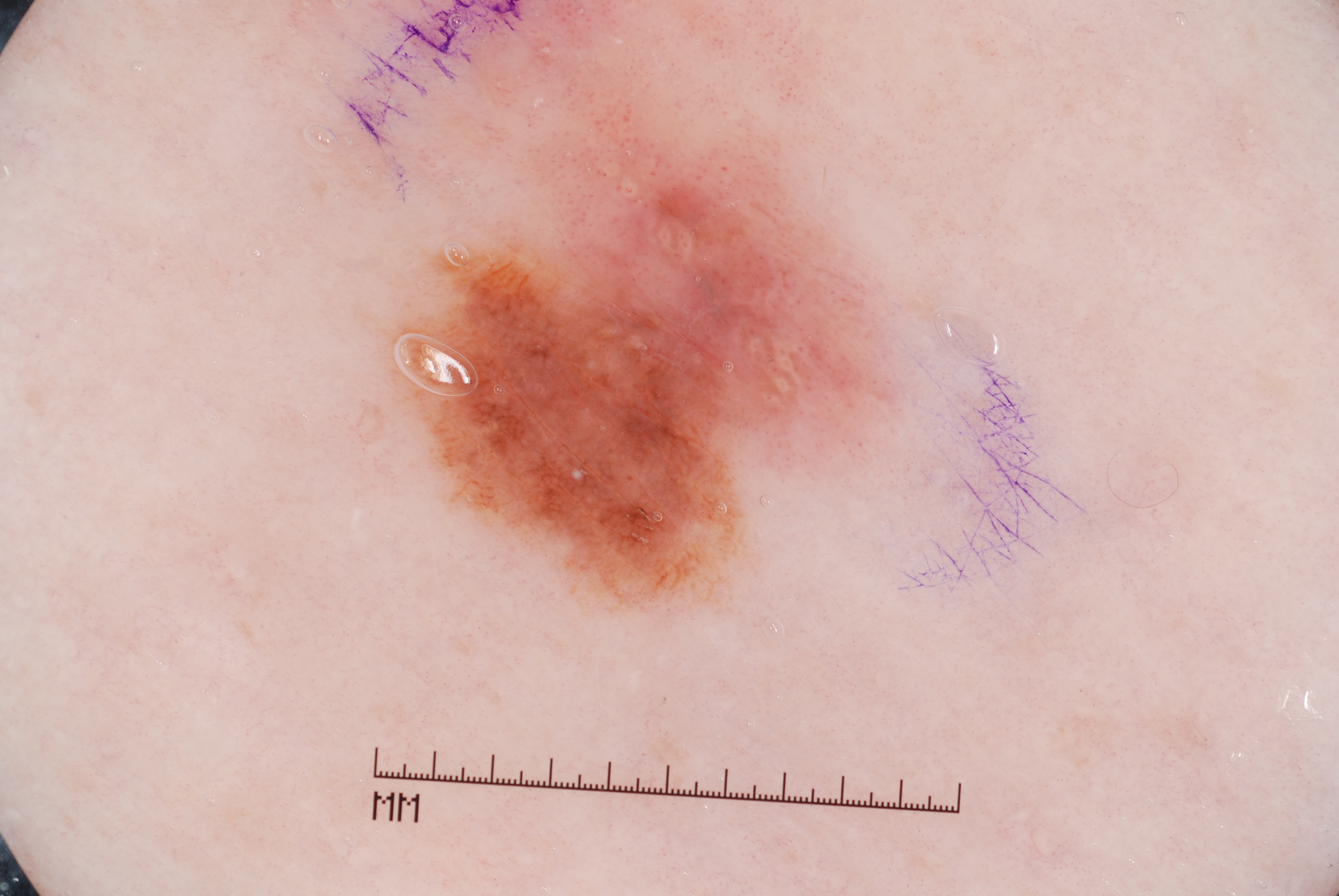Notes:
– image type — dermoscopy
– patient — female, aged 43 to 47
– dermoscopic findings — milia-like cysts
– location — [398, 91, 878, 609]
– lesion size — moderate
– assessment — a melanocytic nevus, a benign lesion